The photograph was taken at an angle, the lesion involves the head or neck and arm: 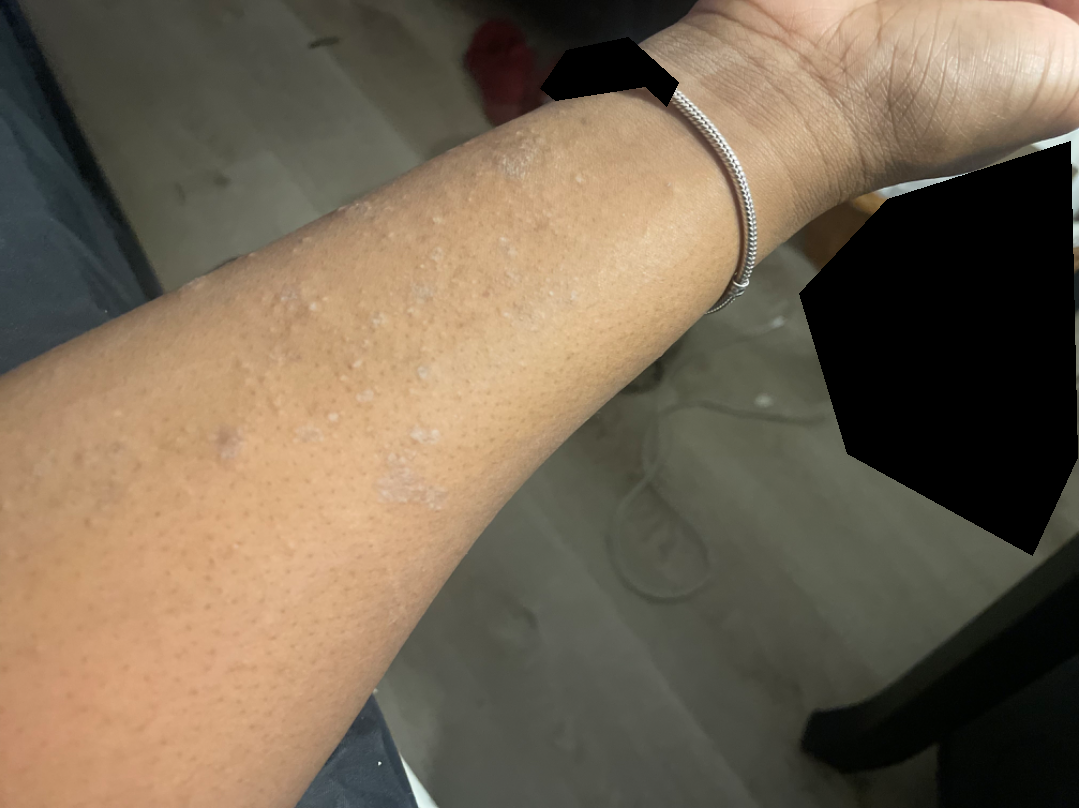| key | value |
|---|---|
| history | one to three months |
| surface texture | rough or flaky |
| clinical impression | Eczema (weight 0.67); Lichen planus/lichenoid eruption (weight 0.33) |